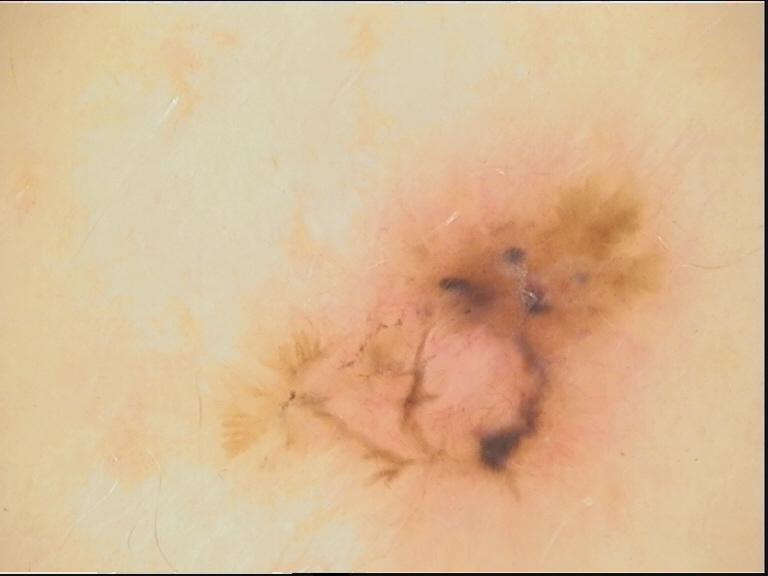The biopsy diagnosis was a basal cell carcinoma.